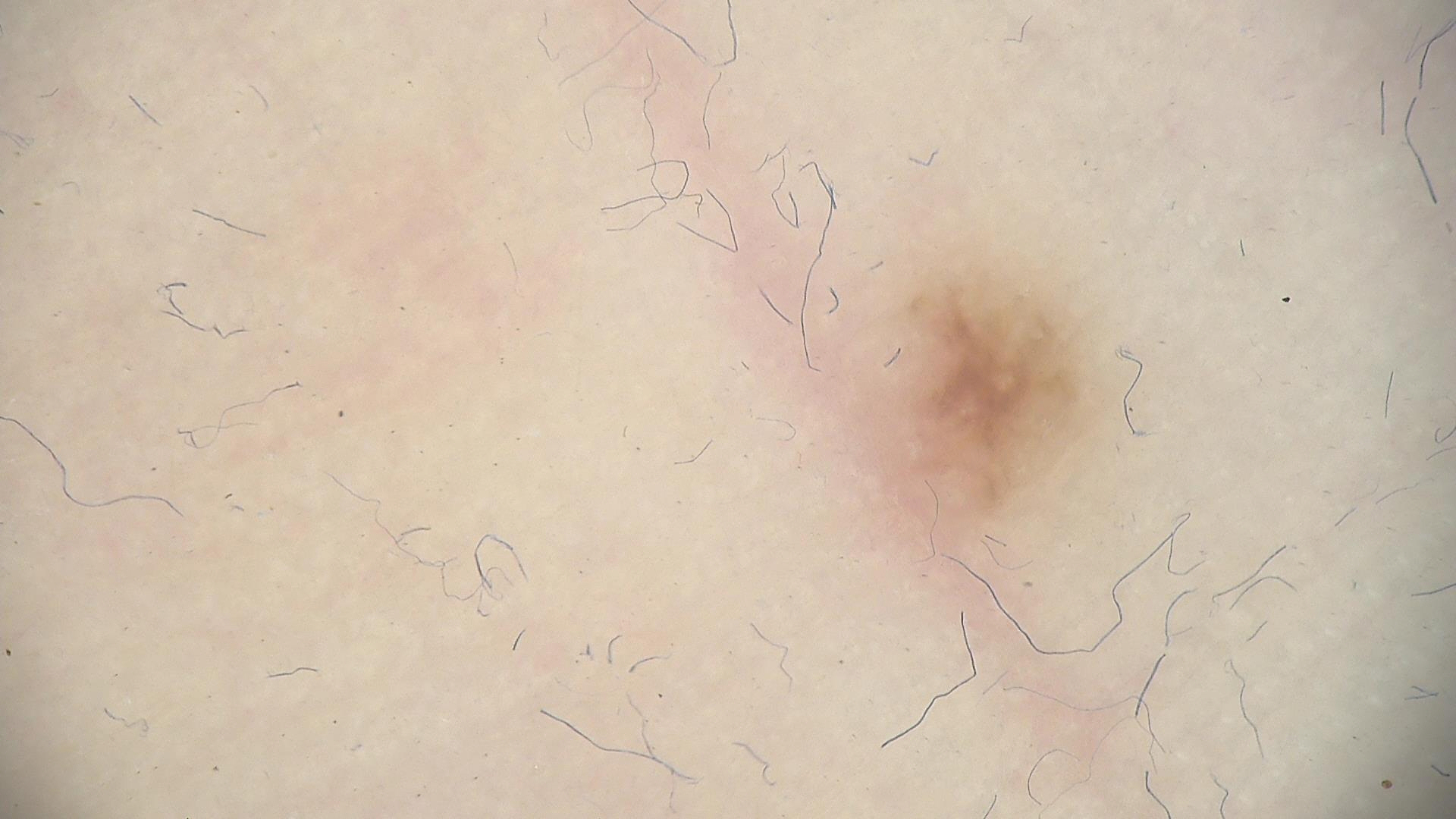Findings: A dermatoscopic image of a skin lesion. Impression: The diagnosis was an acral dysplastic junctional nevus.